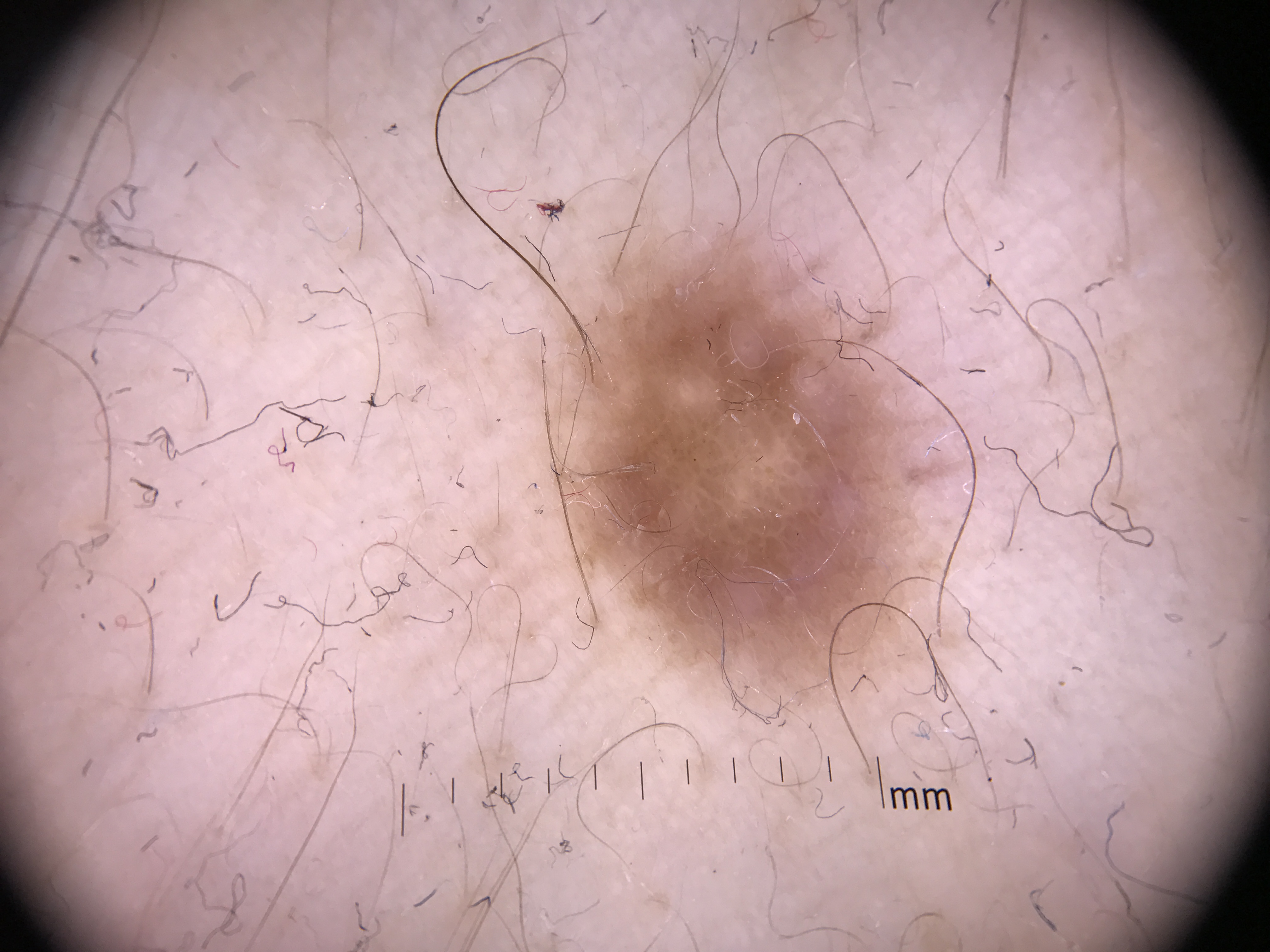Case:
A dermoscopic photograph of a skin lesion.
Impression:
The diagnostic label was a dermatofibroma.